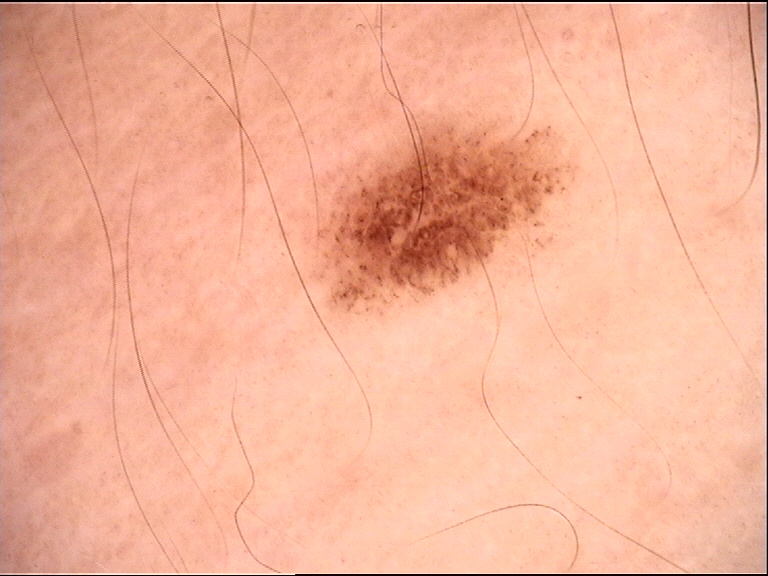<lesion>
  <image>dermoscopy</image>
  <diagnosis>
    <name>dysplastic junctional nevus</name>
    <code>jd</code>
    <malignancy>benign</malignancy>
    <super_class>melanocytic</super_class>
    <confirmation>expert consensus</confirmation>
  </diagnosis>
</lesion>